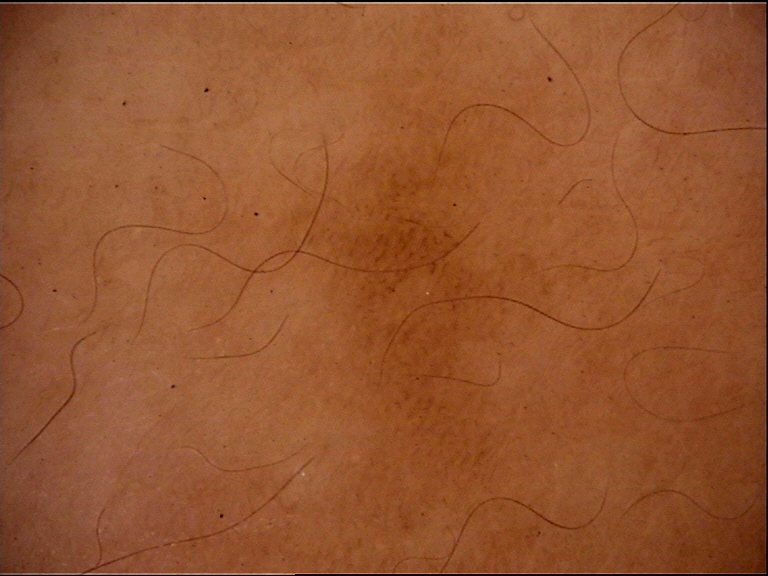Consistent with a dysplastic junctional nevus.